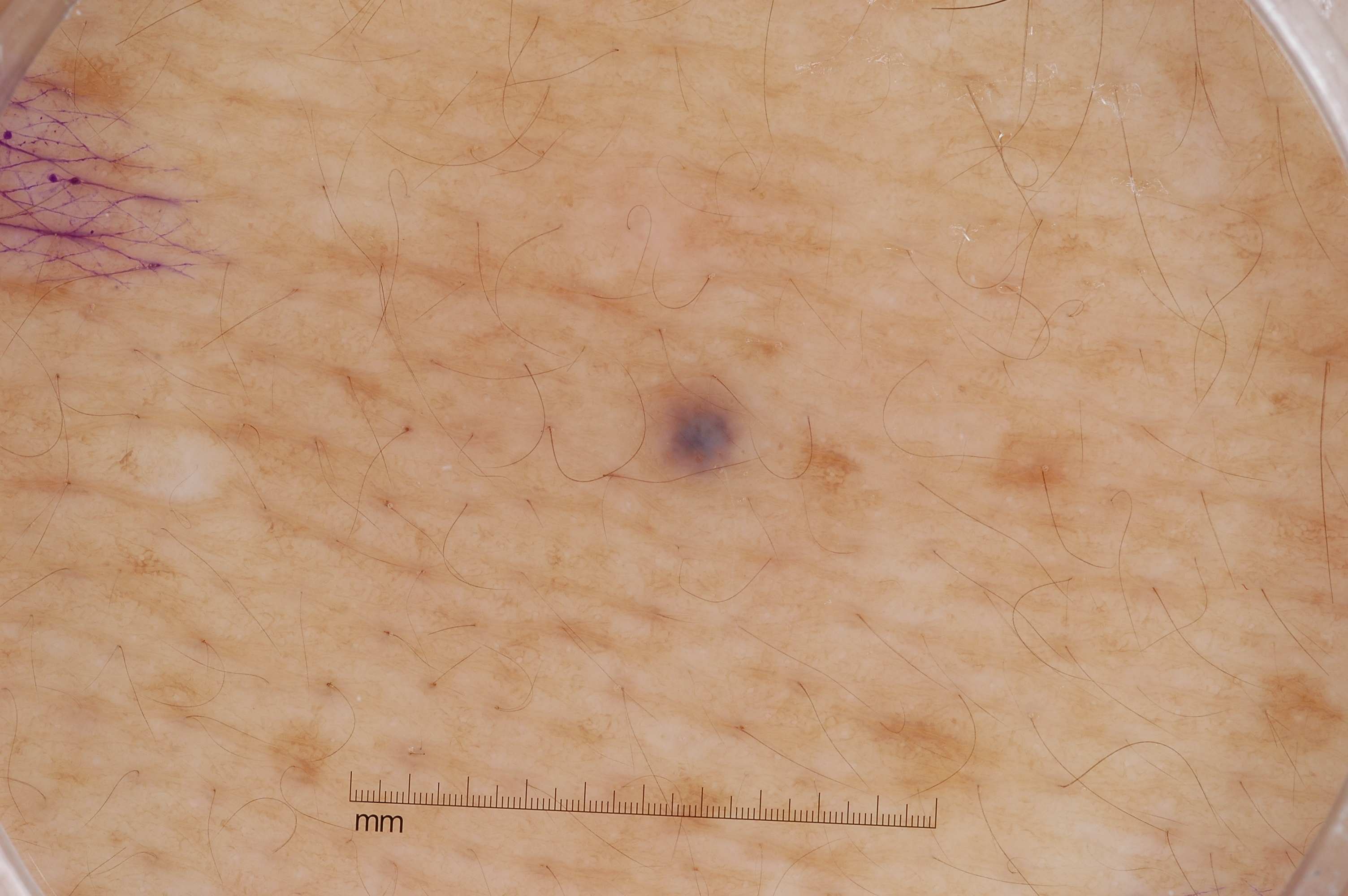subject — male, aged 48-52; image type — dermoscopic image; lesion extent — small; bounding box — 633, 374, 780, 495; absent dermoscopic features — streaks, milia-like cysts, pigment network, and negative network; impression — a melanocytic nevus.